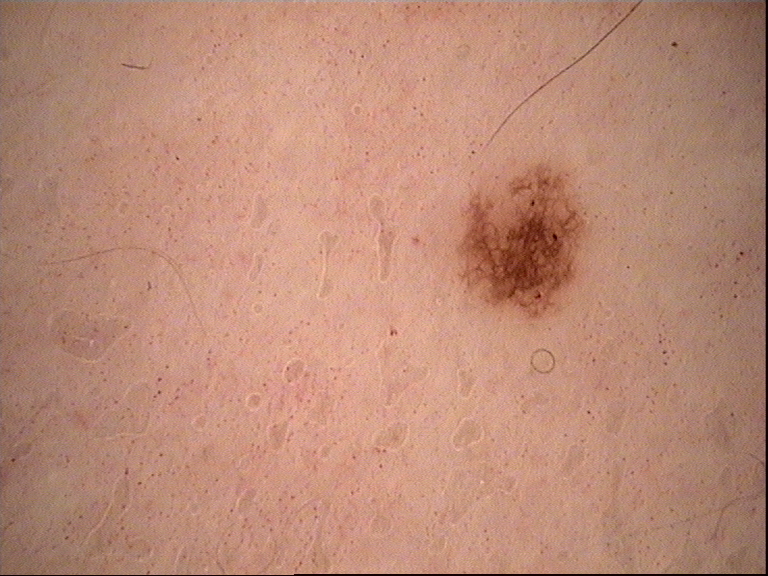Summary:
A dermoscopy image of a single skin lesion.
Conclusion:
The diagnostic label was a benign lesion — a dysplastic junctional nevus.